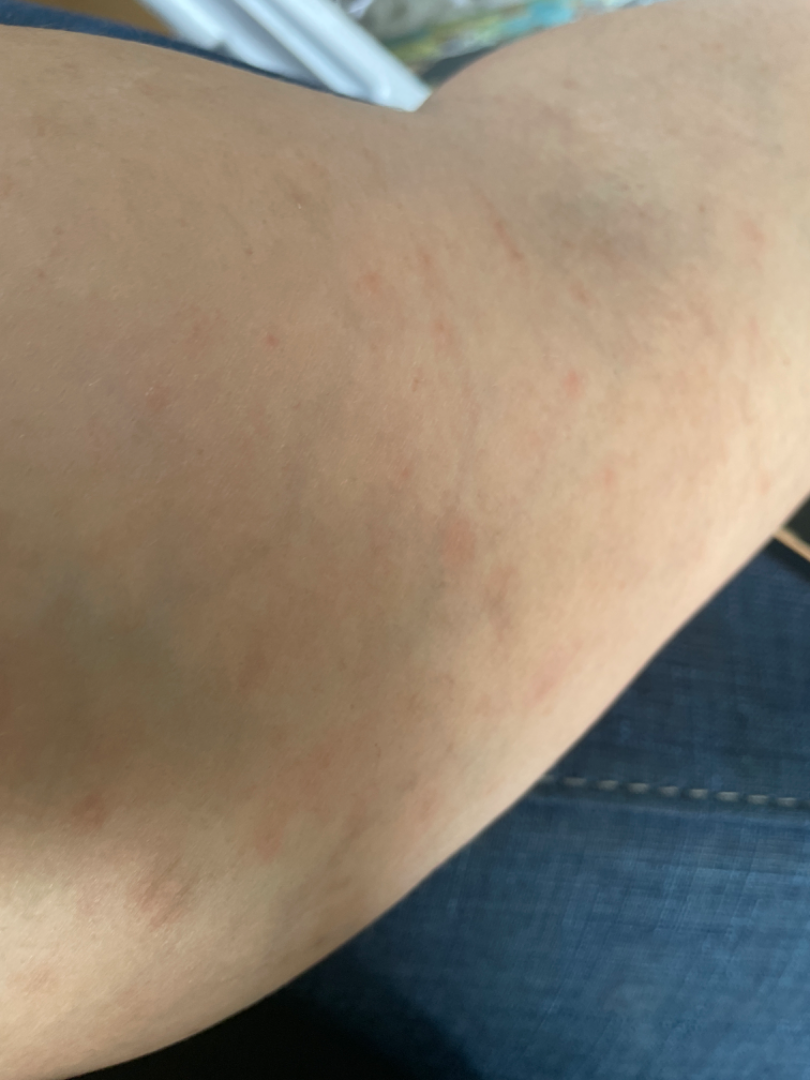Findings:
* assessment · could not be assessed
* framing · at an angle
* symptoms · itching
* site · back of the hand, front of the torso, arm and leg
* patient describes the issue as · a rash
* lesion texture · raised or bumpy
* skin tone · Fitzpatrick phototype II